The affected area is the leg · close-up view:
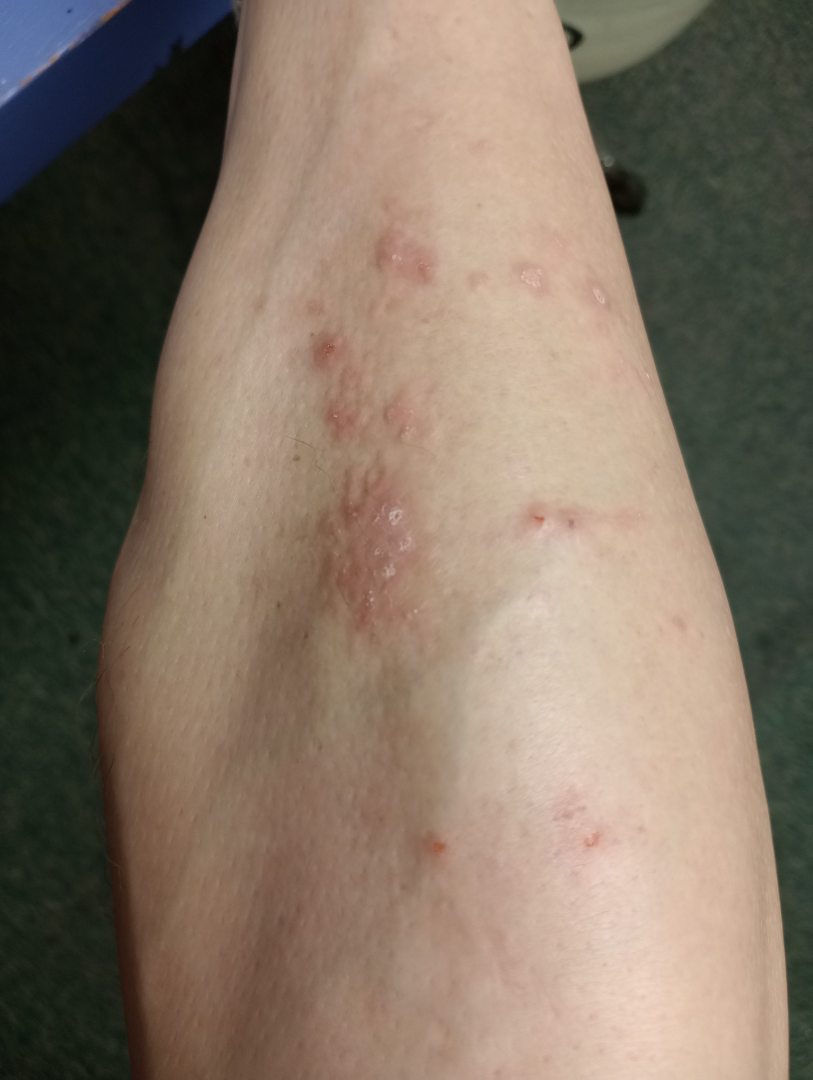Reported duration is one to three months. The lesion is associated with itching. FST II; lay reviewers estimated Monk Skin Tone 2. Self-categorized by the patient as a rash. The lesion is described as raised or bumpy. The differential is split between Insect Bite and Eczema.